A patient age 68 · a clinical close-up photograph of a skin lesion:
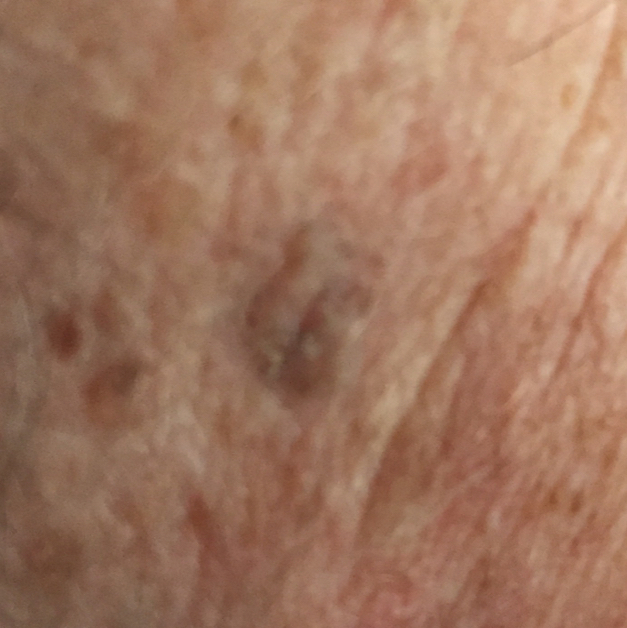Case:
* region · the face
* patient-reported symptoms · elevation
* diagnostic label · seborrheic keratosis (clinical consensus)